Female subject, age 18–29; the affected area is the leg; the patient also reports mouth sores and fatigue; this is a close-up image; self-categorized by the patient as a rash; present for three to twelve months: 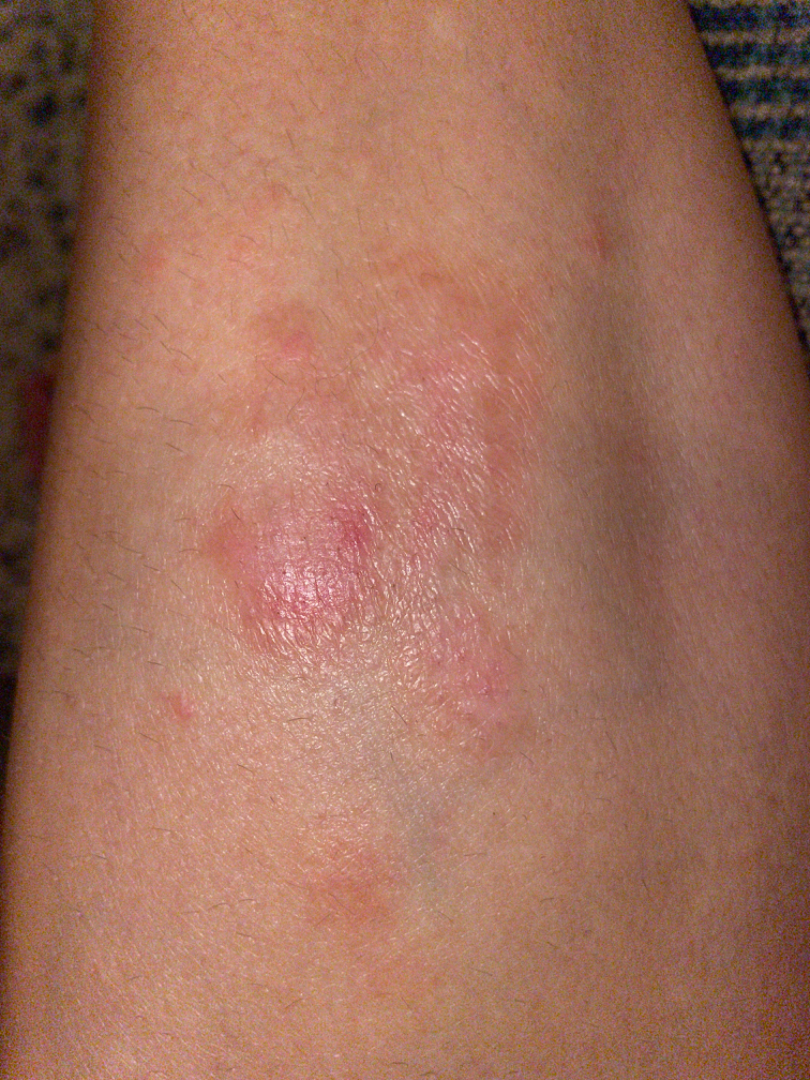| key | value |
|---|---|
| clinical impression | Eczema (considered); Lichen Simplex Chronicus (considered); Lichen planus/lichenoid eruption (less likely); Morphea/Scleroderma (less likely) |